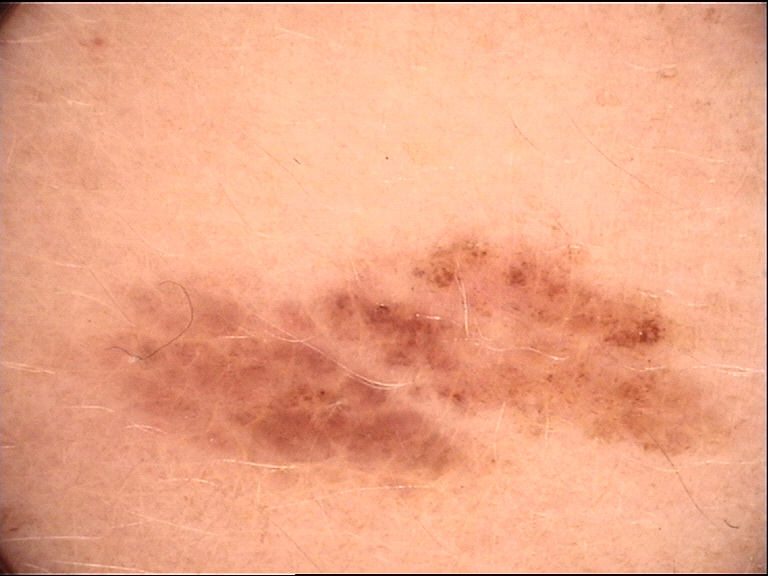| key | value |
|---|---|
| assessment | dysplastic junctional nevus (expert consensus) |